A skin lesion imaged with a dermatoscope — 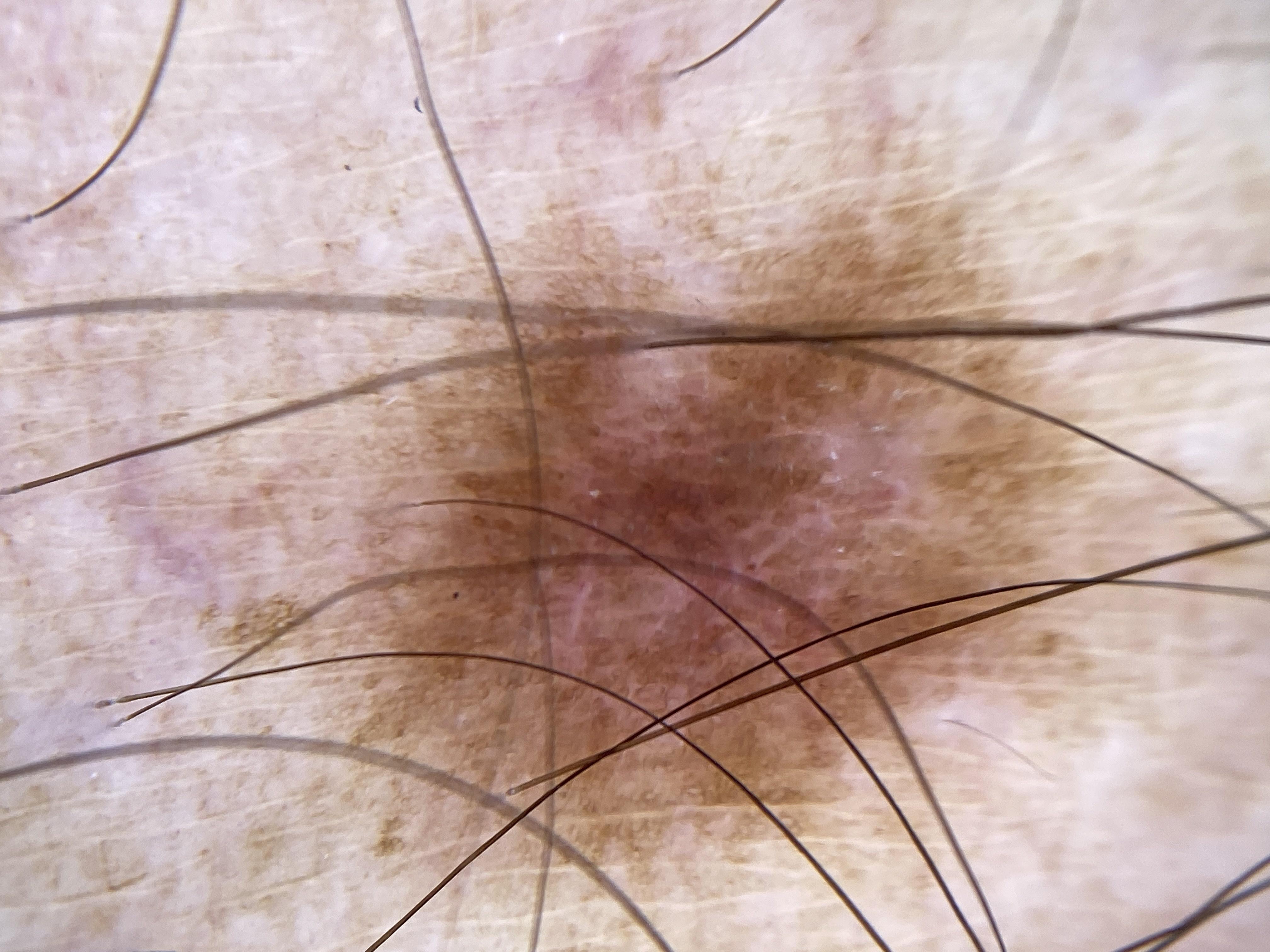Located on the trunk. Expert review favored a nevus.